The patient is a male aged 40–49, located on the arm, a close-up photograph.
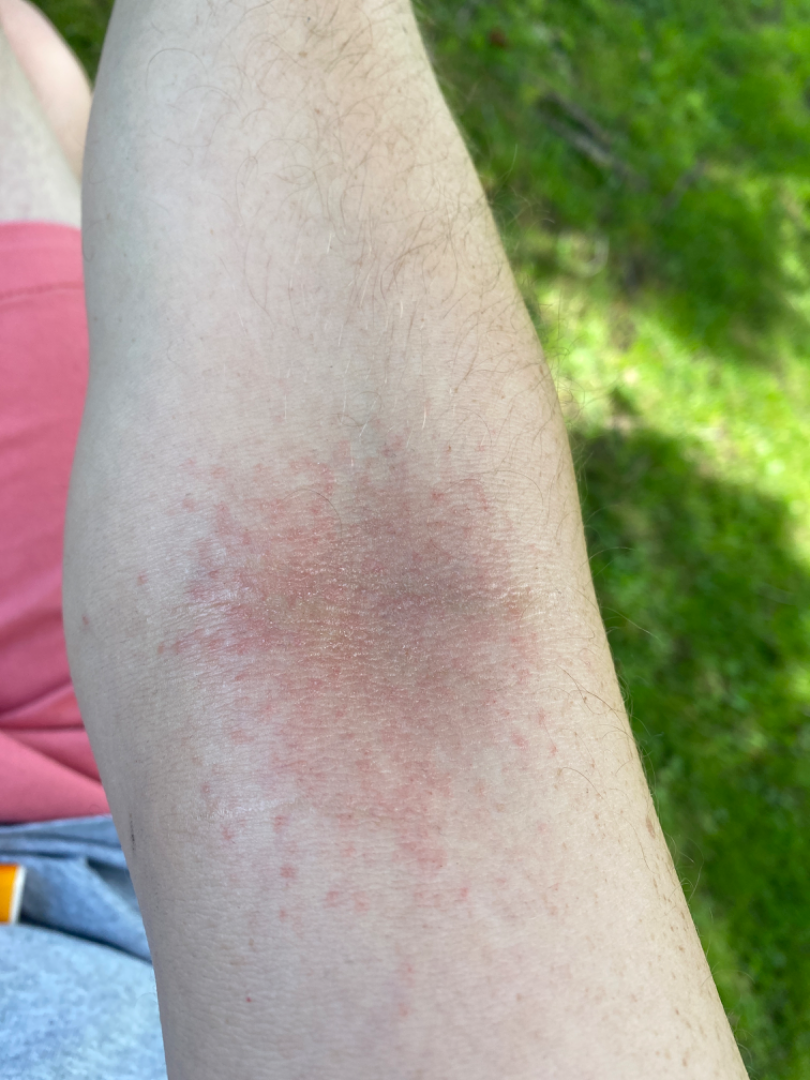On photographic review: Eczema (1.00).